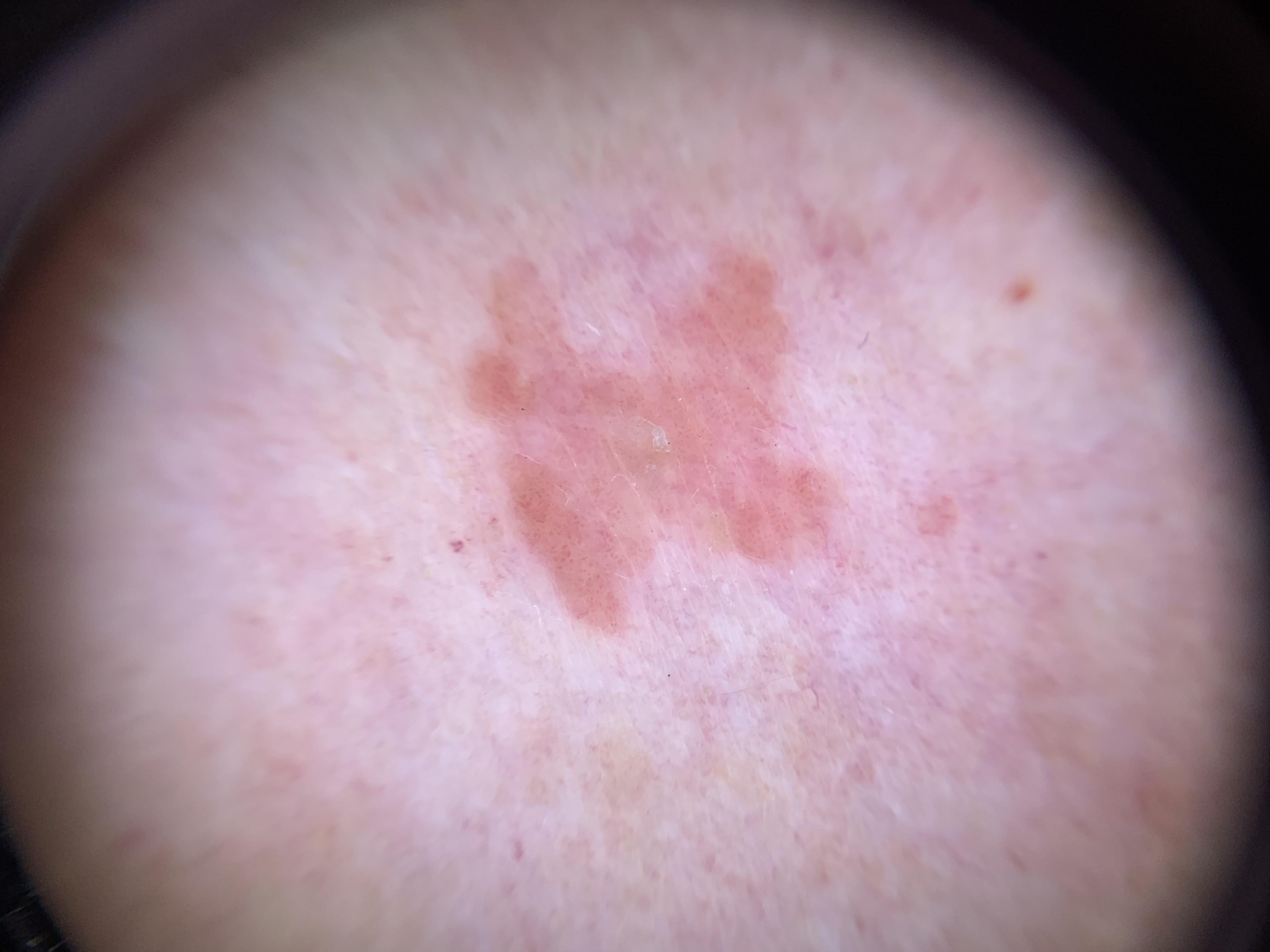A dermatoscopic image of a skin lesion. The patient was assessed as Fitzpatrick phototype II. A male patient in their mid-60s. The lesion is on the trunk, specifically the anterior trunk. Histopathology confirmed a lesion of epidermal origin — a squamous cell carcinoma.